Close-up view. Skin tone: FST I; lay reviewers estimated Monk Skin Tone 2 (US pool) or 1 (India pool):
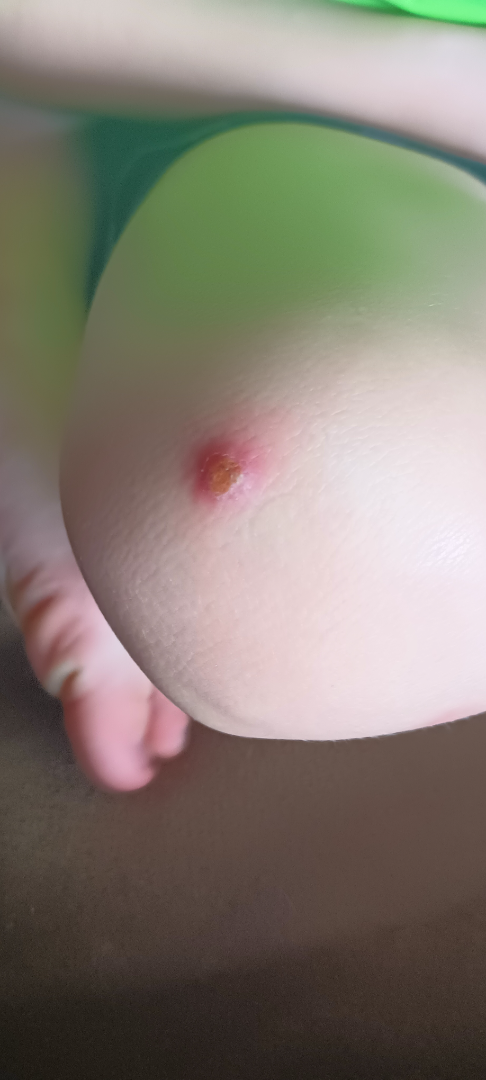- clinical impression · the favored diagnosis is Impetigo; possibly Herpes Simplex